The palm and arm are involved; the photo was captured at a distance — 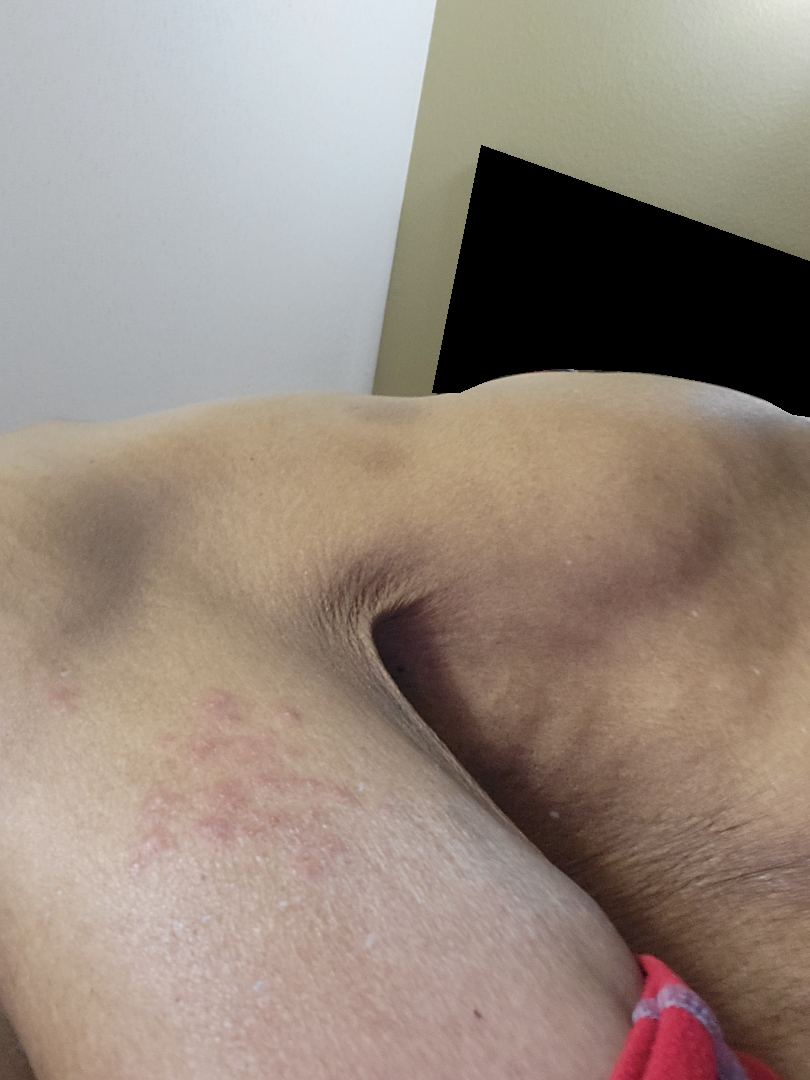assessment = not assessable.